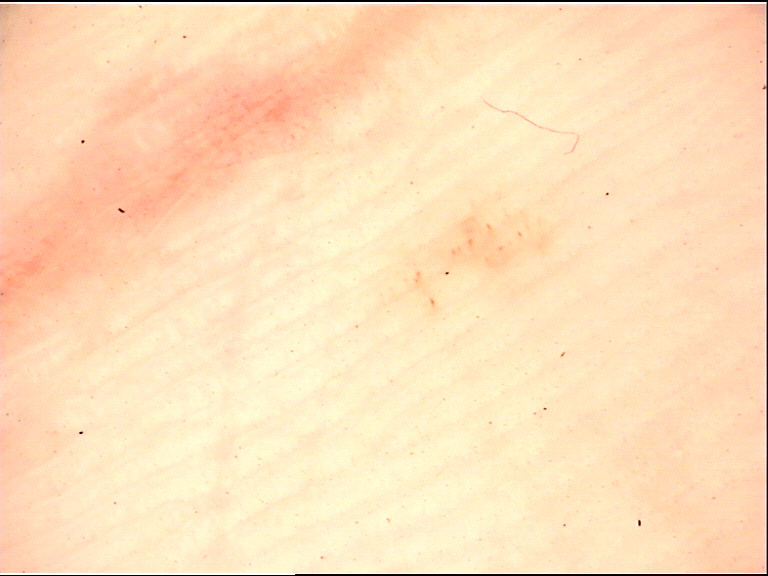<dermoscopy>
<image>dermoscopy</image>
<diagnosis>
<name>acral junctional nevus</name>
<code>ajb</code>
<malignancy>benign</malignancy>
<super_class>melanocytic</super_class>
<confirmation>expert consensus</confirmation>
</diagnosis>
</dermoscopy>